A dermoscopic image of a skin lesion: 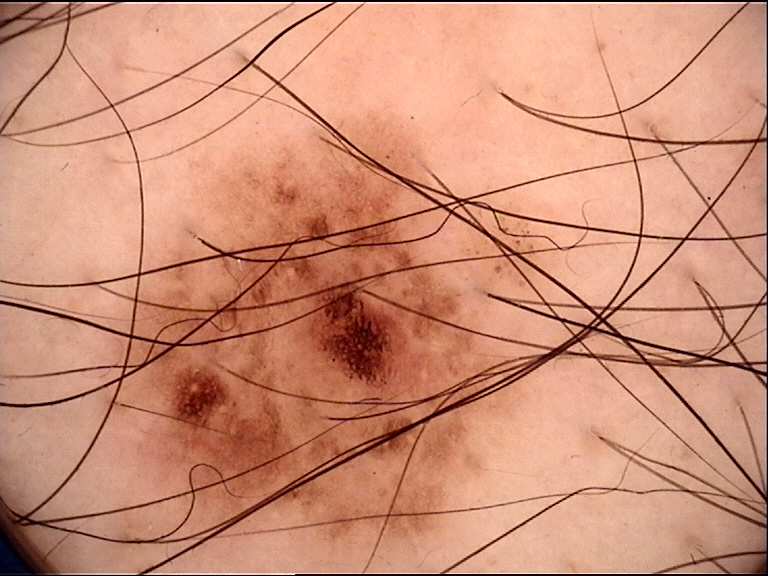Labeled as a benign lesion — a dysplastic junctional nevus.